A dermatoscopic image of a skin lesion:
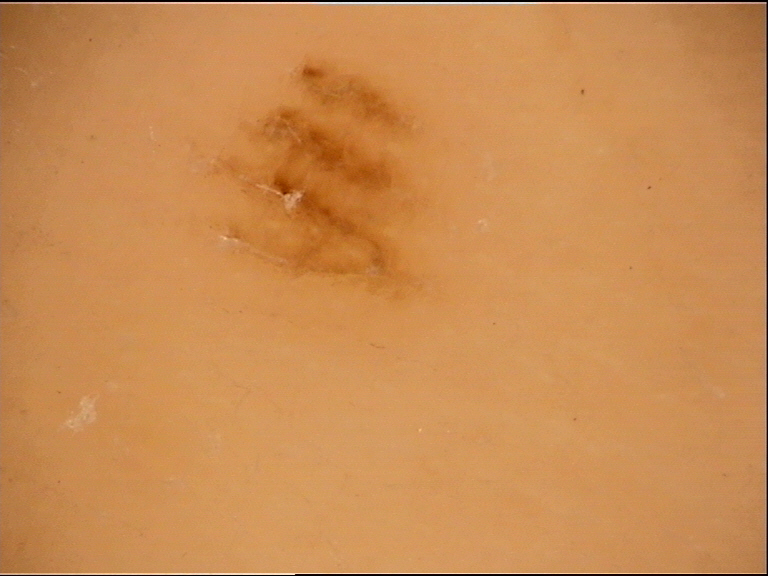label = acral junctional nevus (expert consensus).